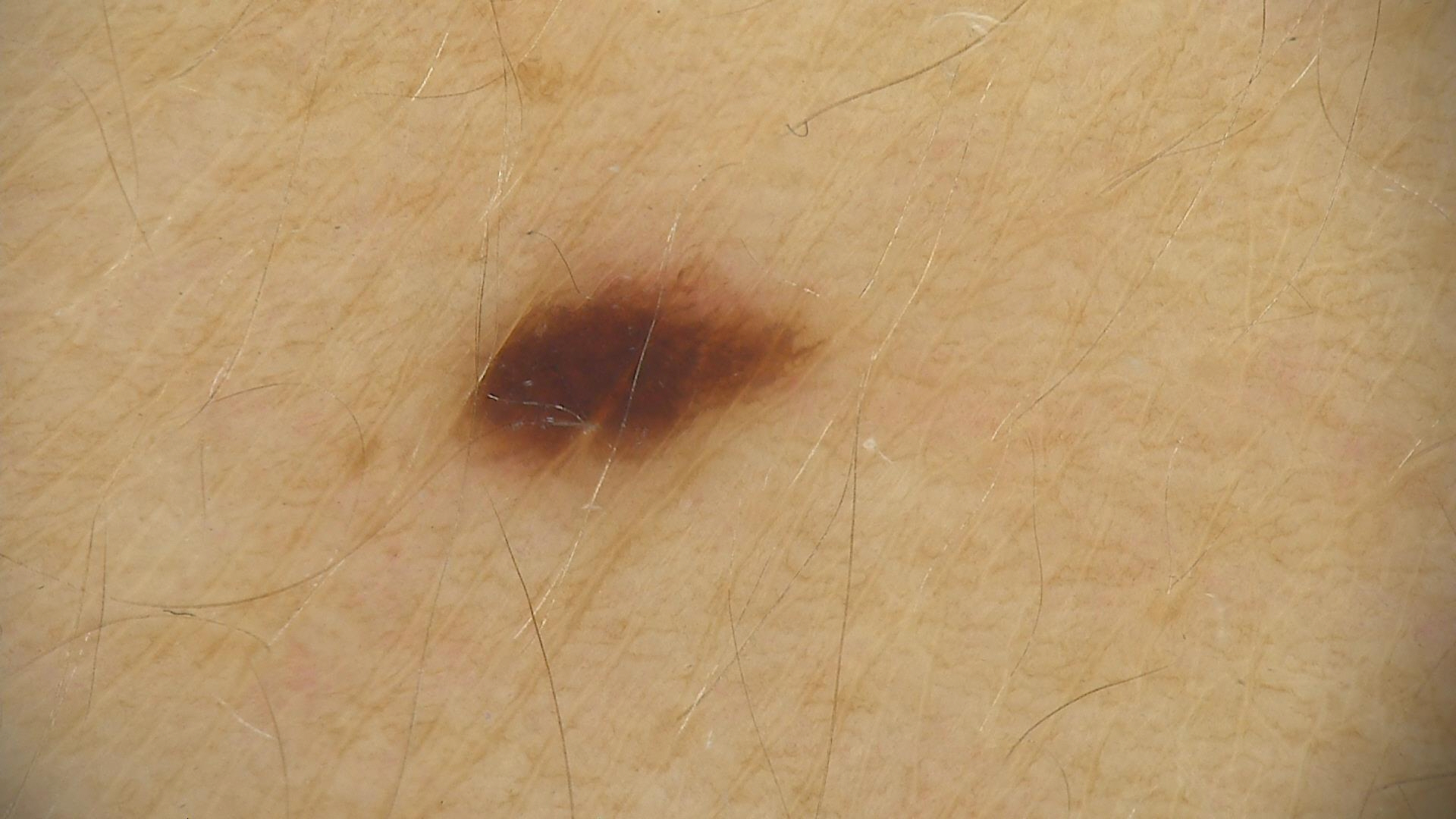Case: A dermoscopic close-up of a skin lesion. Conclusion: Diagnosed as a benign lesion — a dysplastic junctional nevus.